A dermoscopic close-up of a skin lesion:
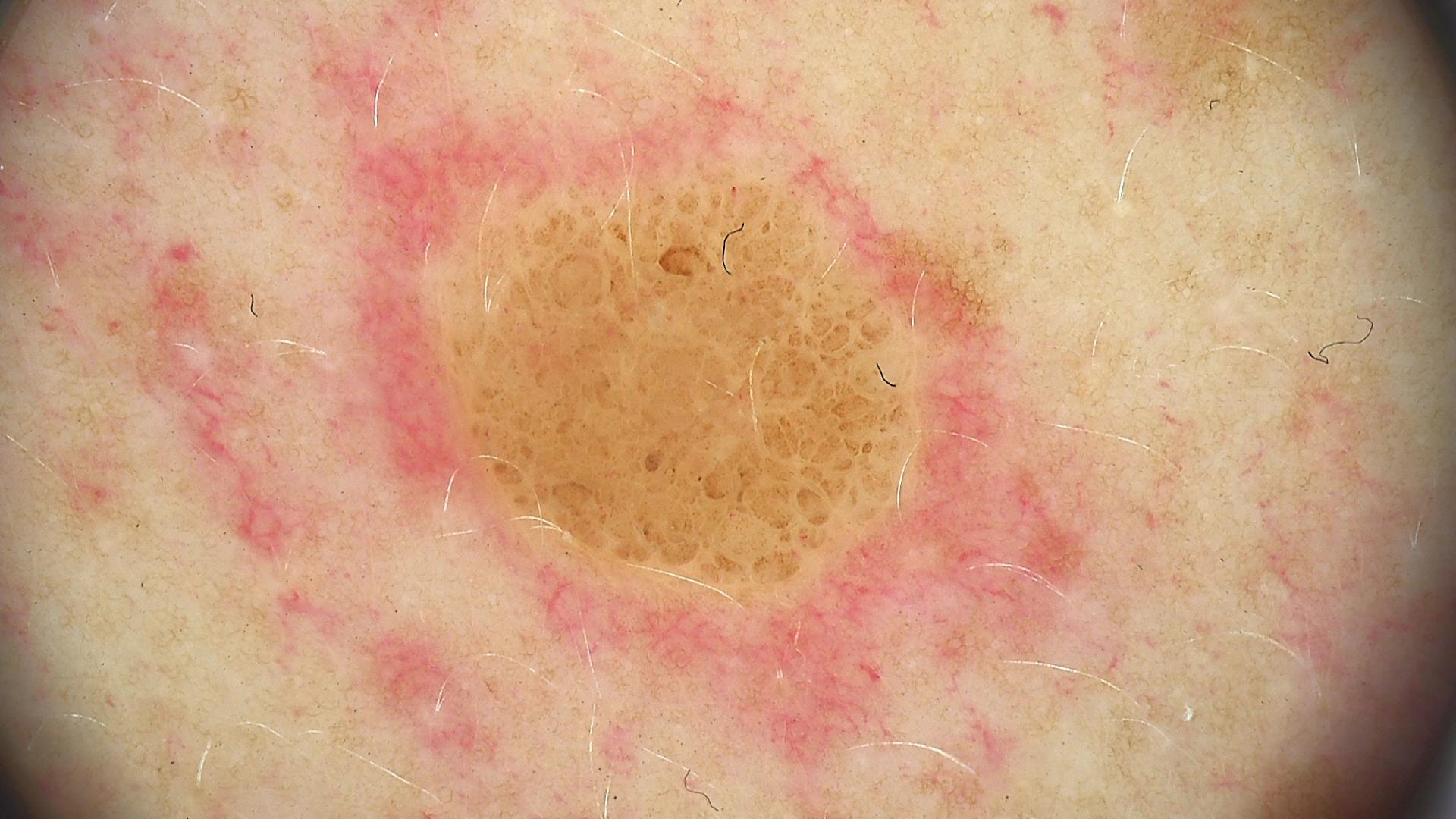Consistent with a banal lesion — a compound nevus.